A male subject, aged 63-67 · a dermoscopy image of a single skin lesion — 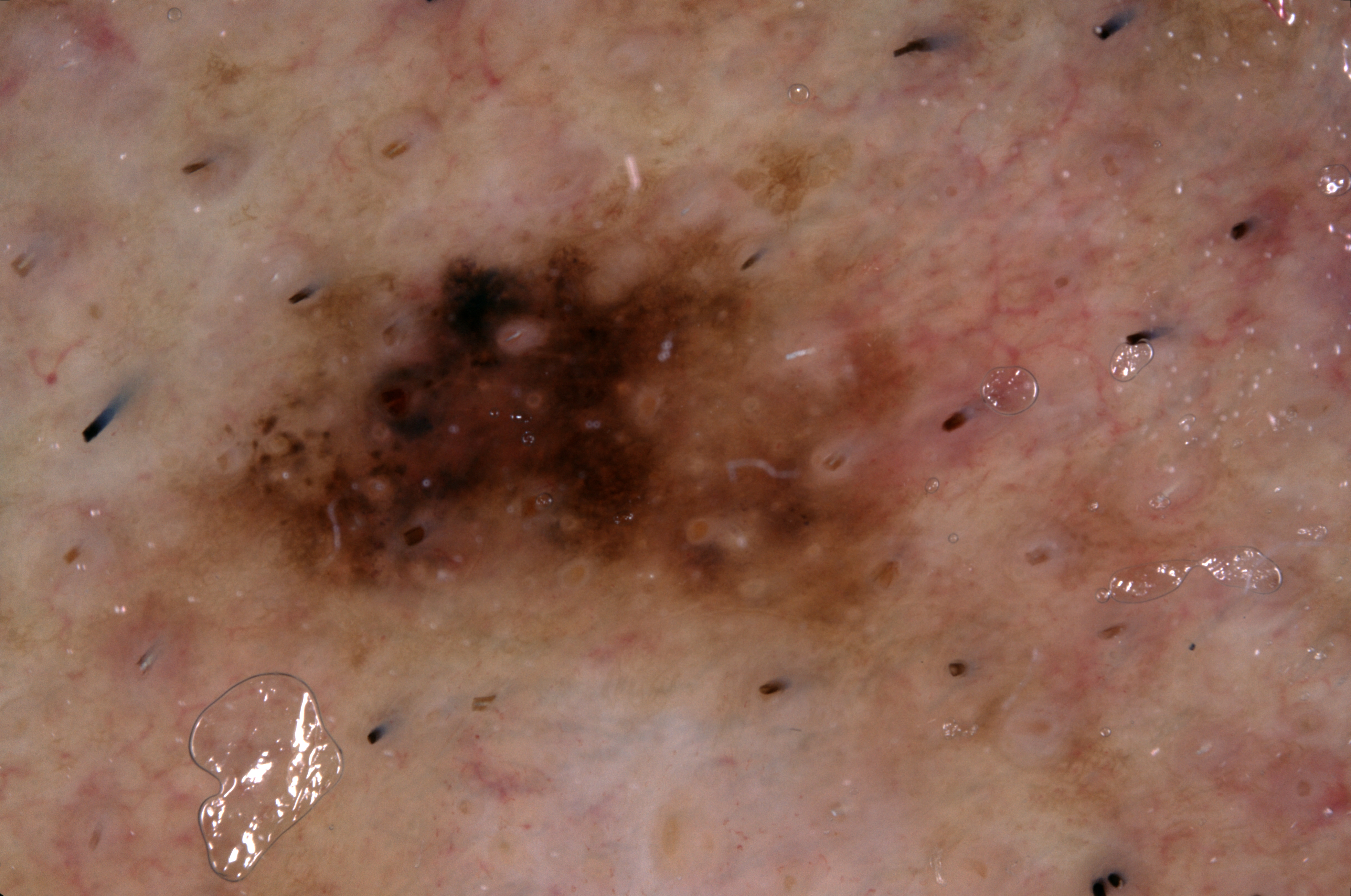Findings: The lesion is located at 146/174/970/689. Dermoscopically, the lesion shows milia-like cysts and pigment network. Diagnosis: Histopathologically confirmed as a melanoma, a skin cancer.